A dermoscopic image of a skin lesion:
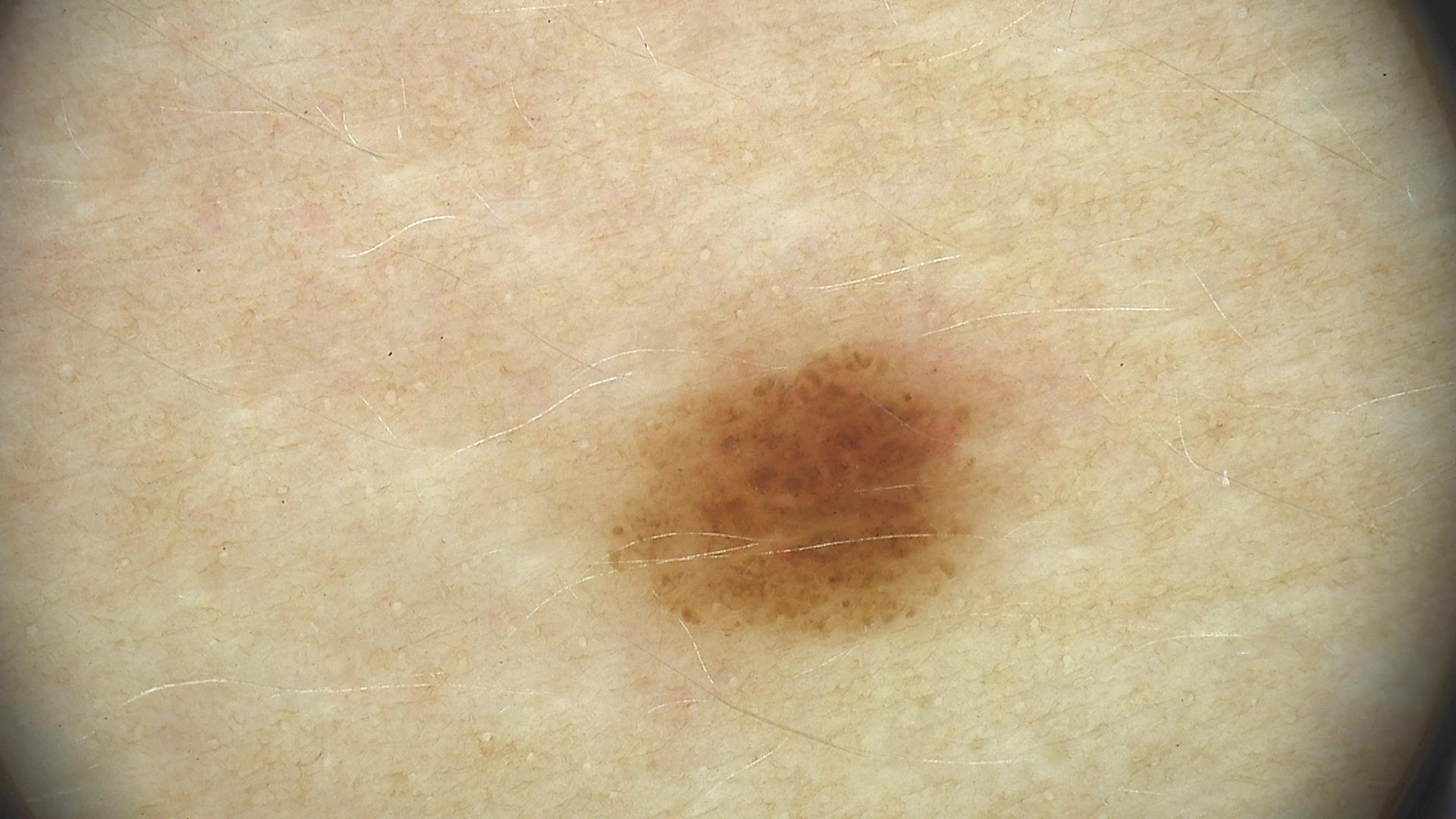class: dysplastic junctional nevus (expert consensus).